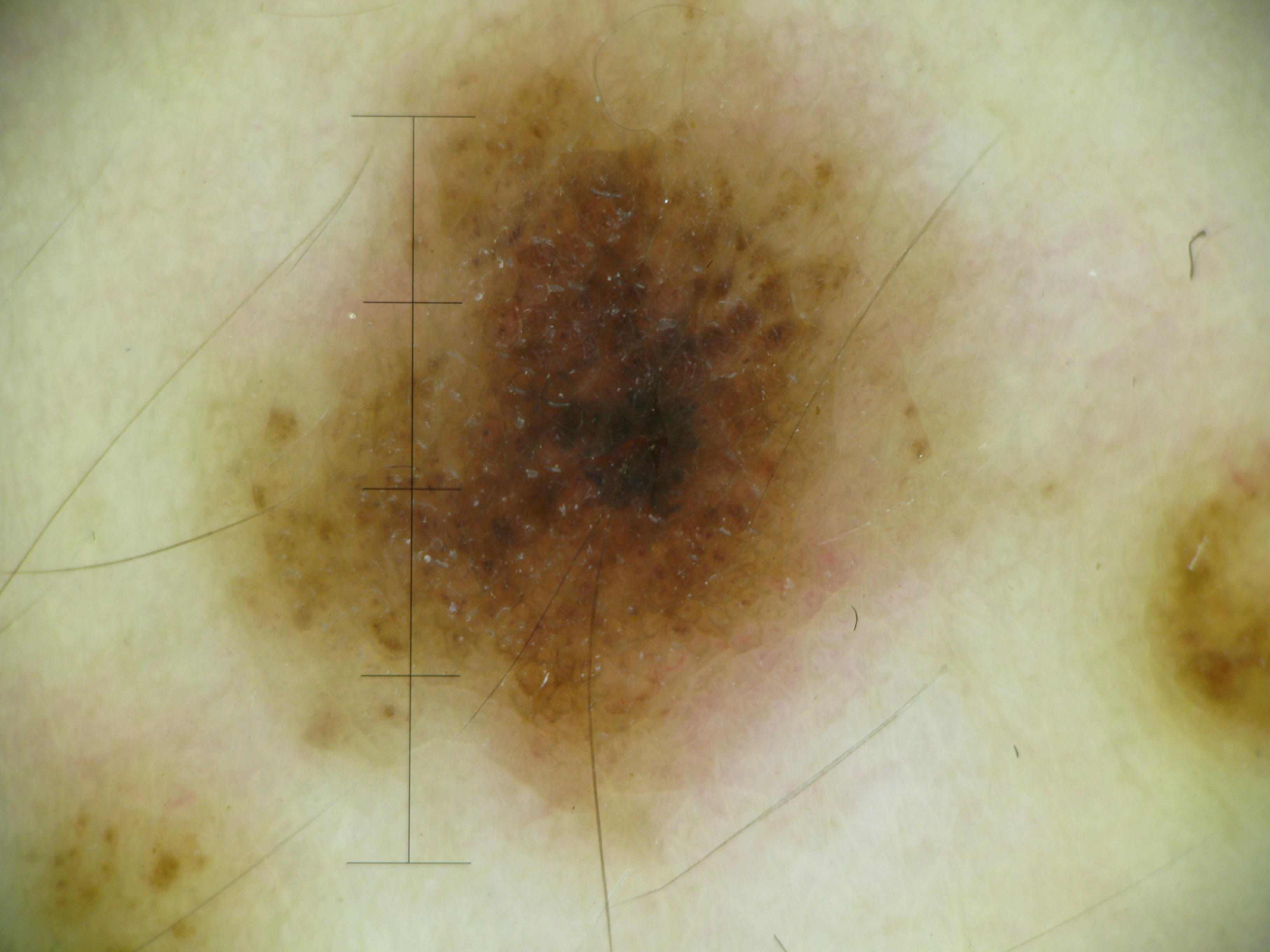Labeled as a benign lesion — a dysplastic junctional nevus.